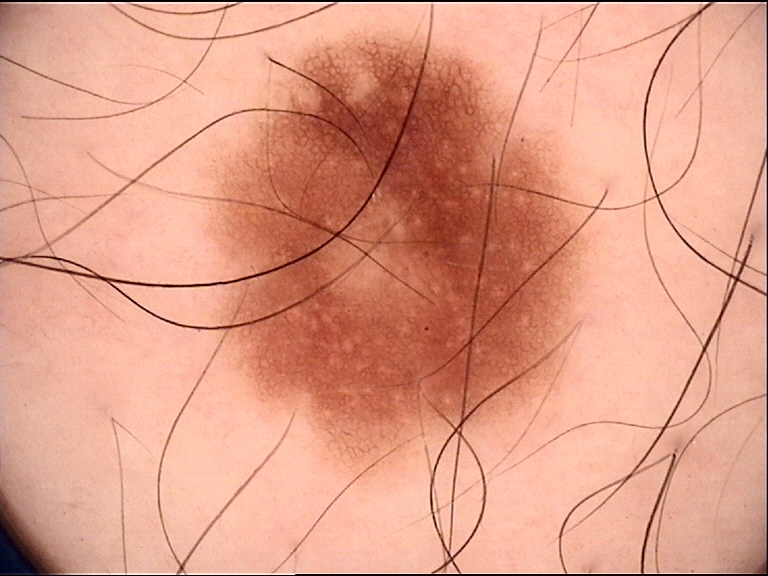A dermoscopy image of a single skin lesion.
Classified as a benign lesion — a dysplastic junctional nevus.